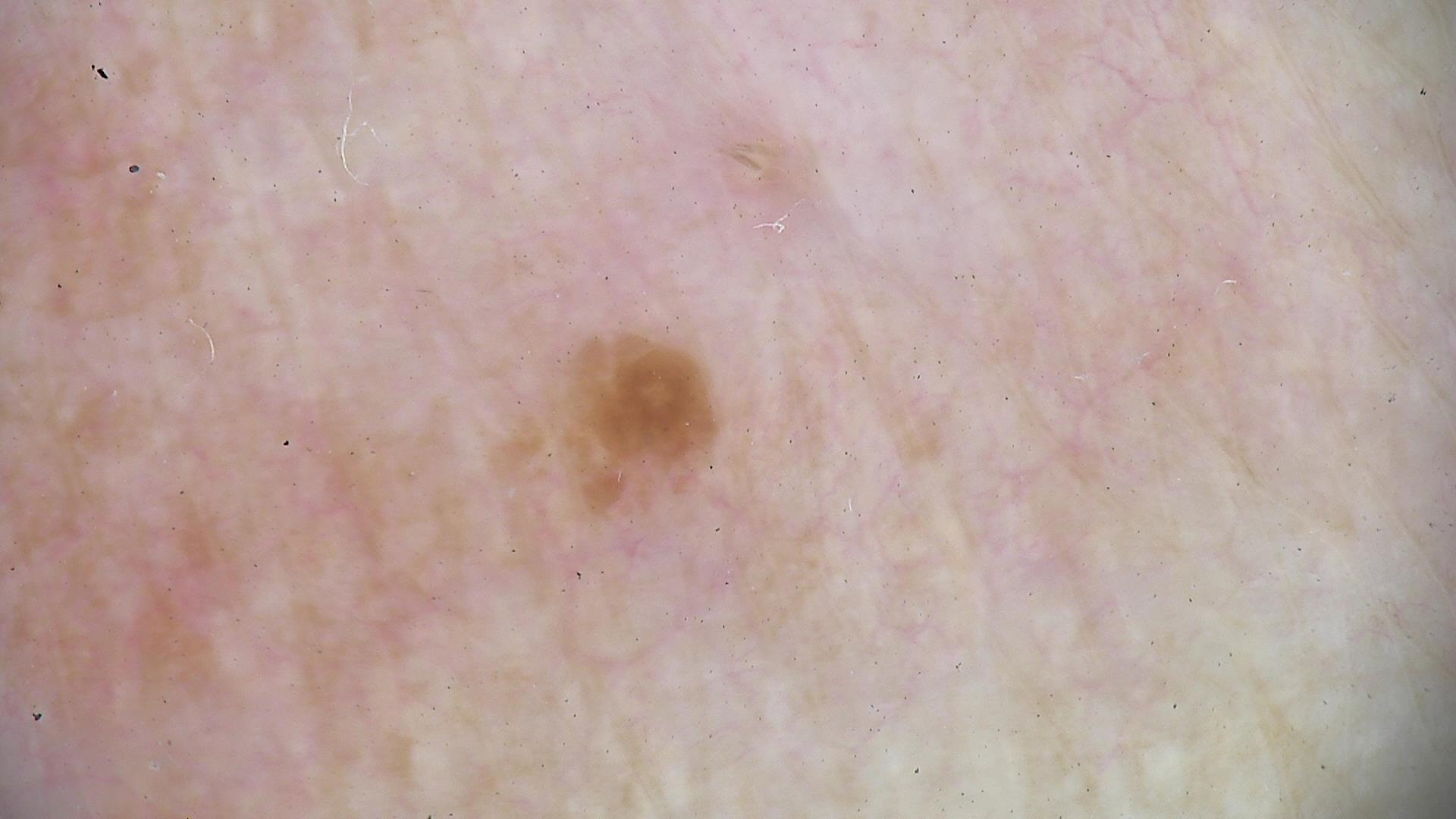{"diagnosis": {"name": "junctional nevus", "code": "jb", "malignancy": "benign", "super_class": "melanocytic", "confirmation": "expert consensus"}}